Dermoscopy of a skin lesion, the subject is a male aged approximately 45 — 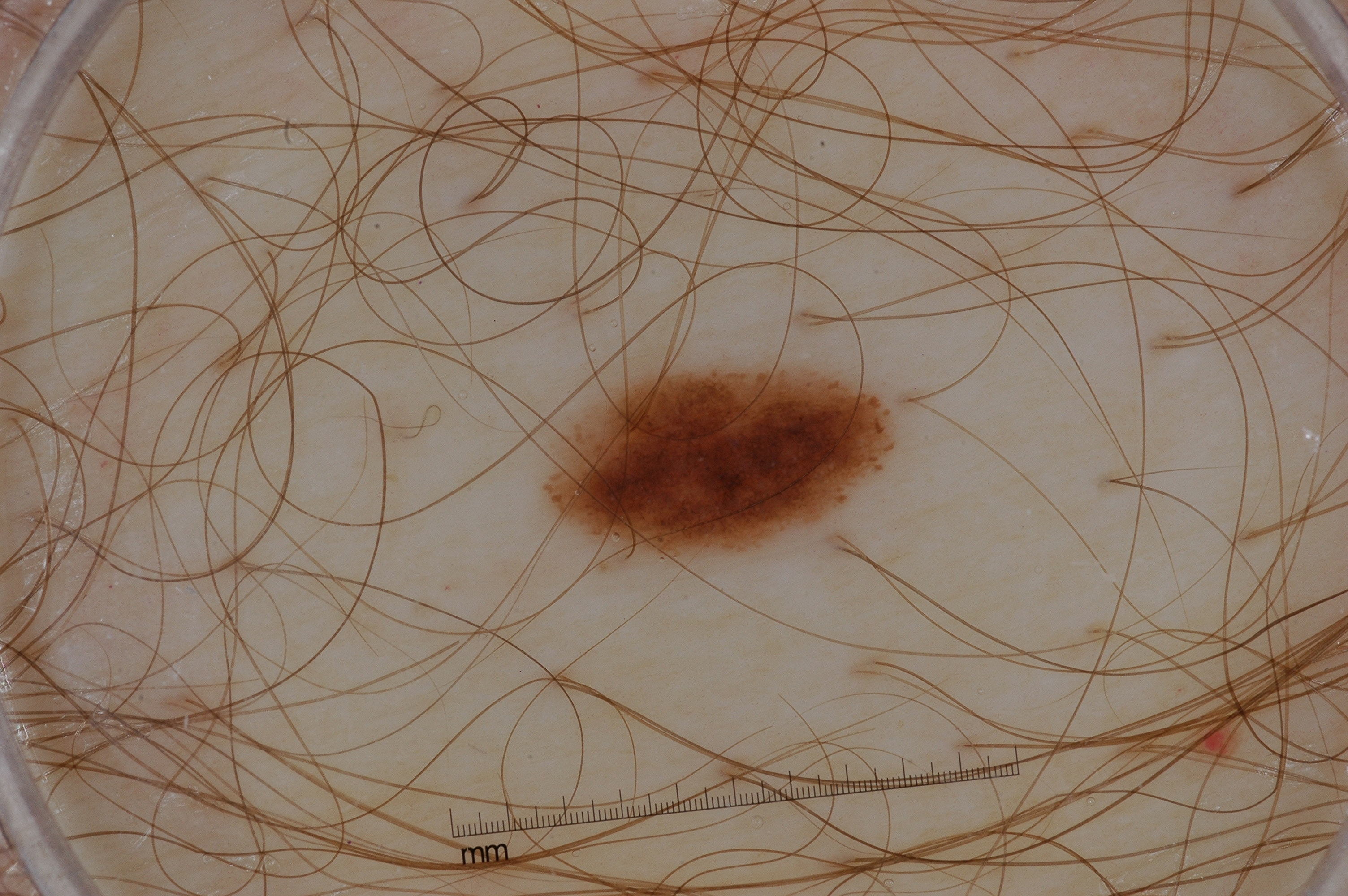Case summary:
Dermoscopic review identifies pigment network and streaks, with no milia-like cysts or negative network. With coordinates (x1, y1, x2, y2), the visible lesion spans (558, 371, 895, 553).
Conclusion:
The clinical diagnosis was a melanocytic nevus, a benign skin lesion.